The lesion is associated with itching · present for about one day · no relevant systemic symptoms · the photo was captured at an angle · male contributor, age 18–29 · located on the back of the hand · the patient considered this a rash · the patient indicates the lesion is fluid-filled and raised or bumpy.
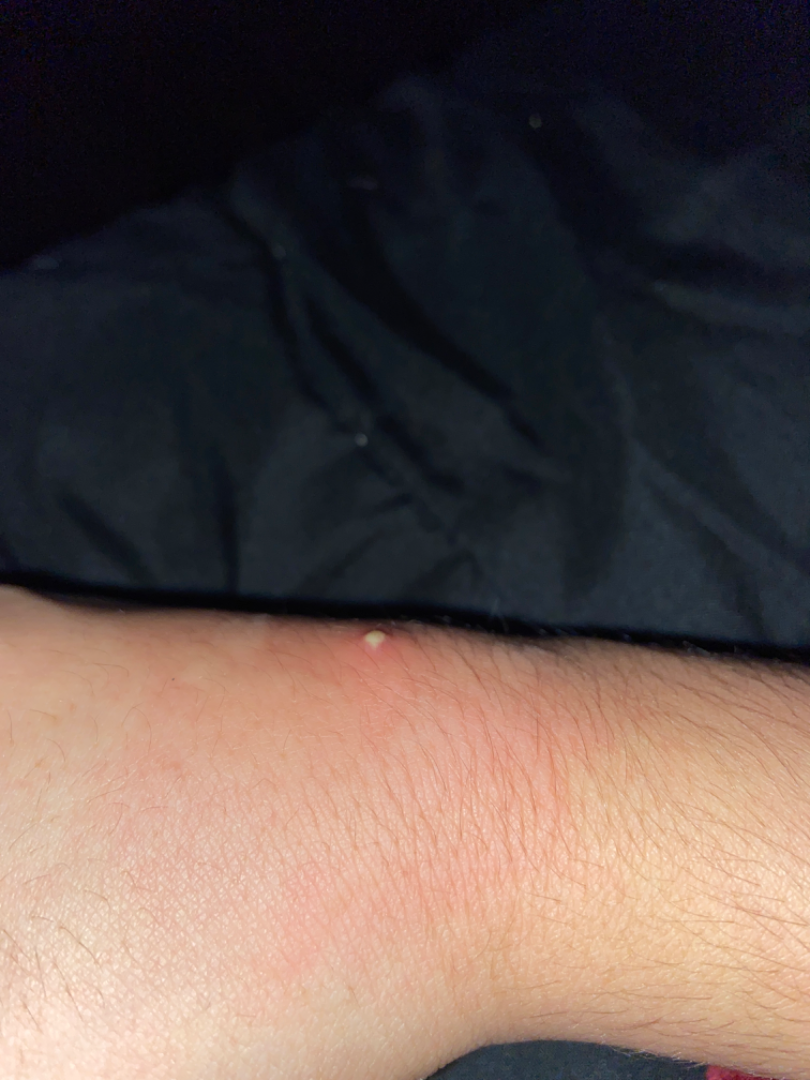diagnostic considerations = the differential, in no particular order, includes Cellulitis and Insect Bite; possibly Abscess; less probable is pustules